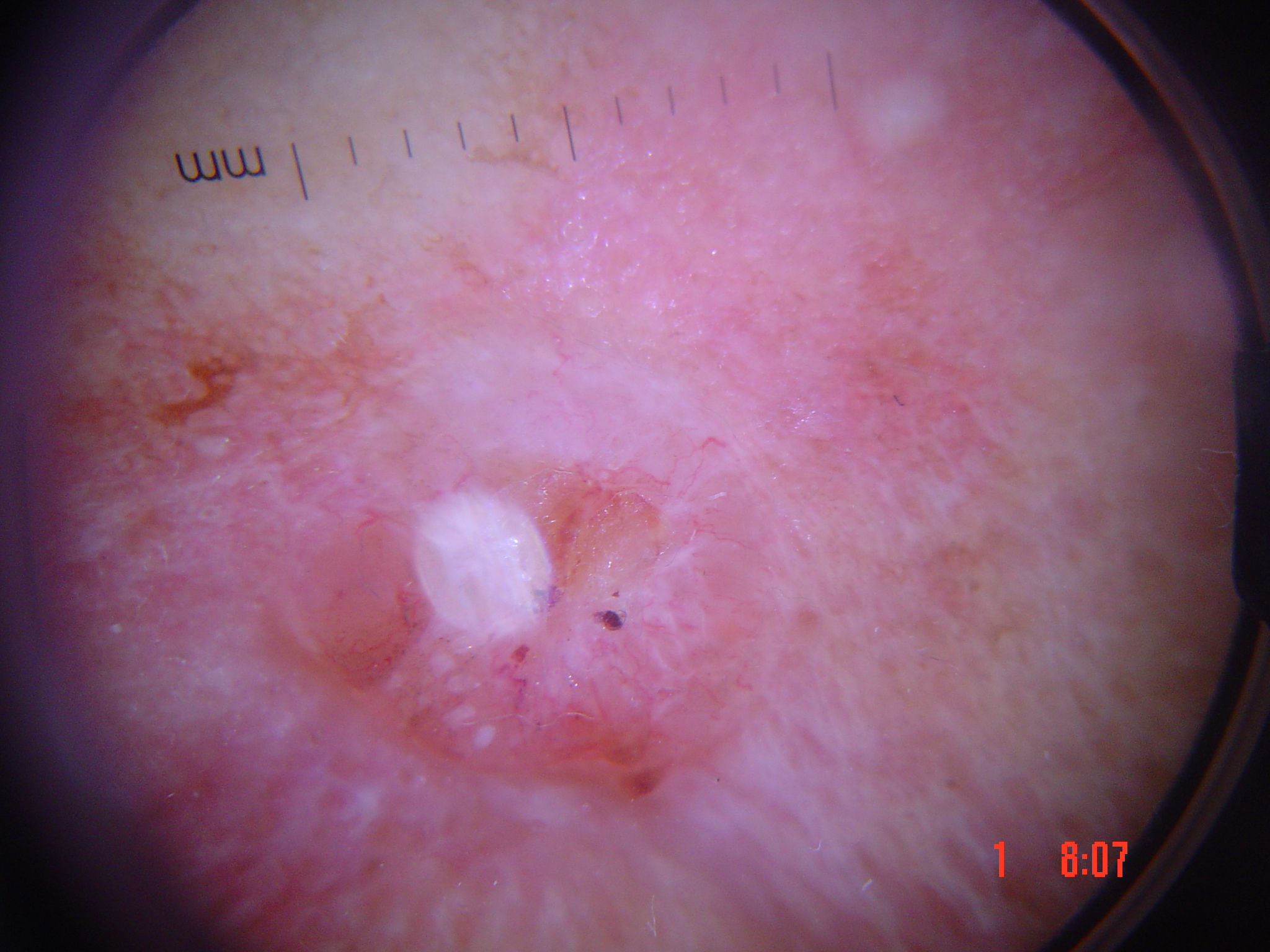{
  "image": "dermatoscopy",
  "diagnosis": {
    "name": "basal cell carcinoma",
    "code": "bcc",
    "malignancy": "malignant",
    "super_class": "non-melanocytic",
    "confirmation": "histopathology"
  }
}